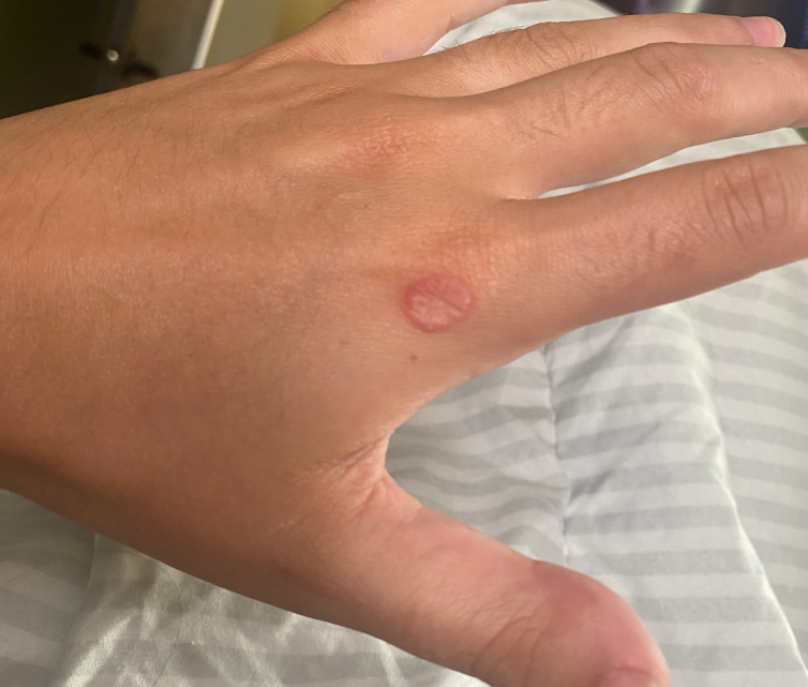| feature | finding |
|---|---|
| shot type | at a distance |
| anatomic site | back of the hand |
| dermatologist impression | Verruca vulgaris (leading); Granuloma annulare (considered); Lichen planus/lichenoid eruption (considered) |